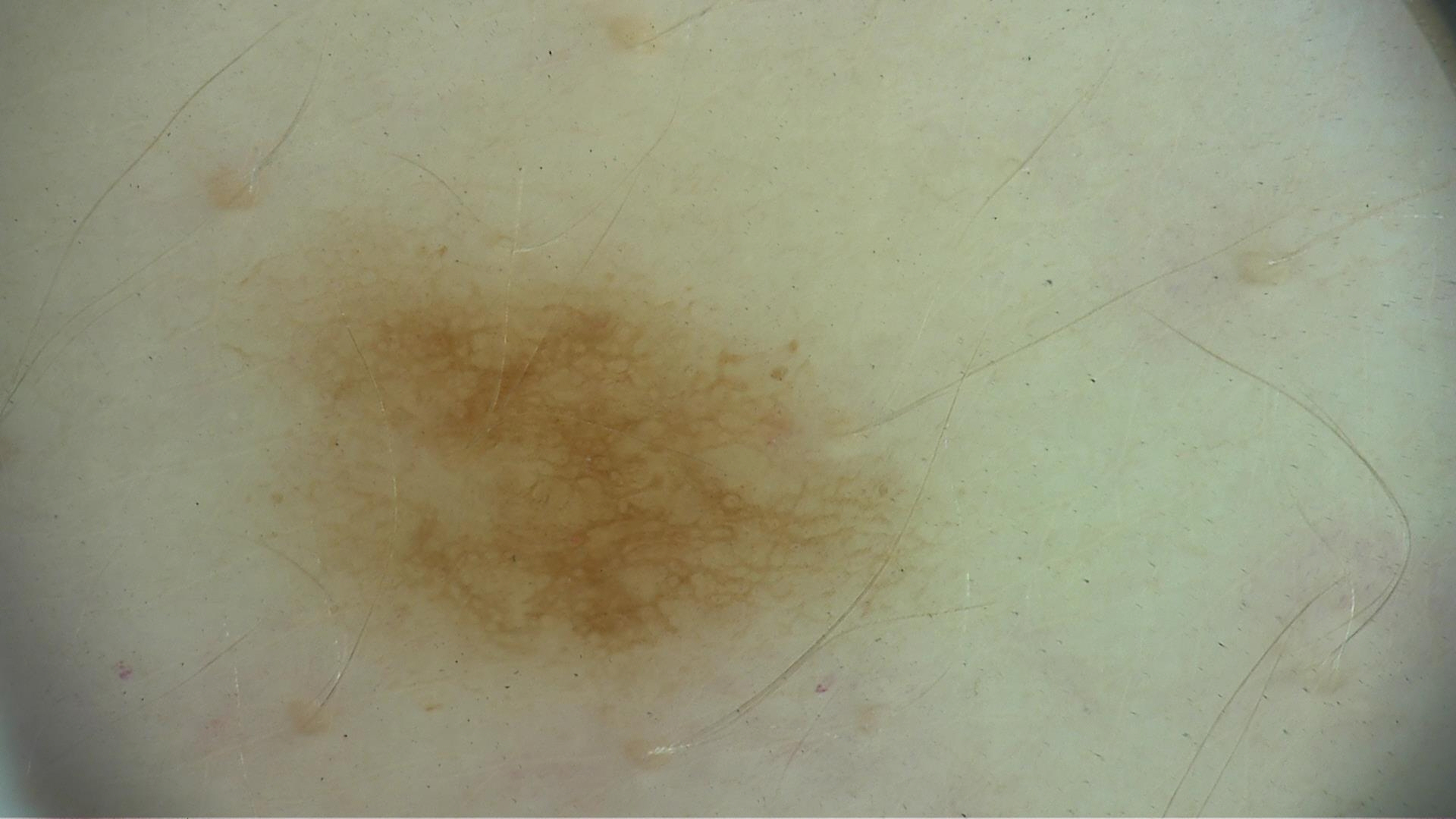assessment=dysplastic junctional nevus (expert consensus).